The patient says their skin reddens with sun exposure · the patient reports a personal history of skin cancer · a moderate number of moles by the patient's own estimate · the referring clinician suspected melanoma · a skin lesion imaged with a dermatoscope · a female subject 50 years old:
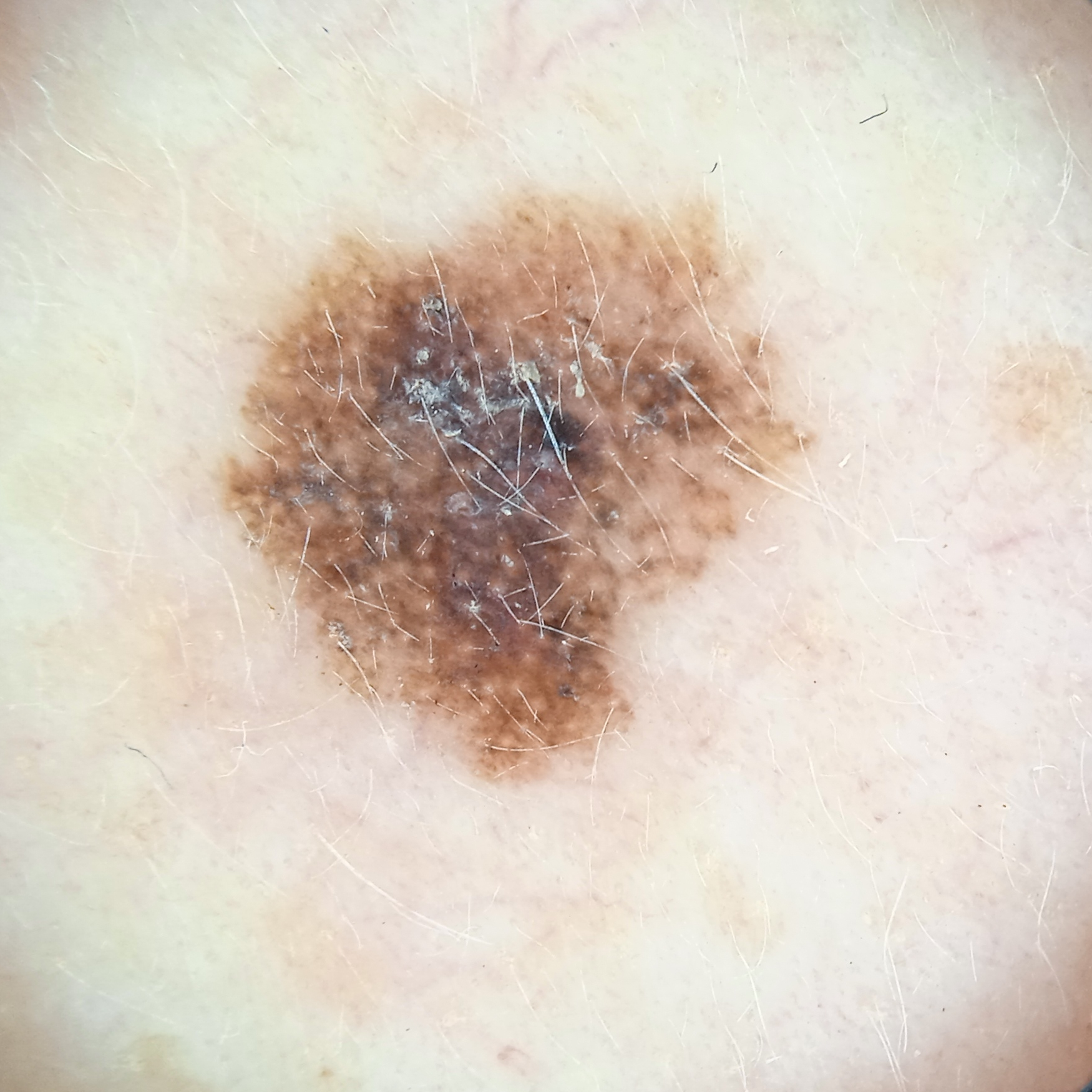Findings:
The lesion involves the face. The lesion is about 7 mm across.
Conclusion:
Confirmed on histopathology as a melanoma, following excision, with Breslow depth 0.4 mm.